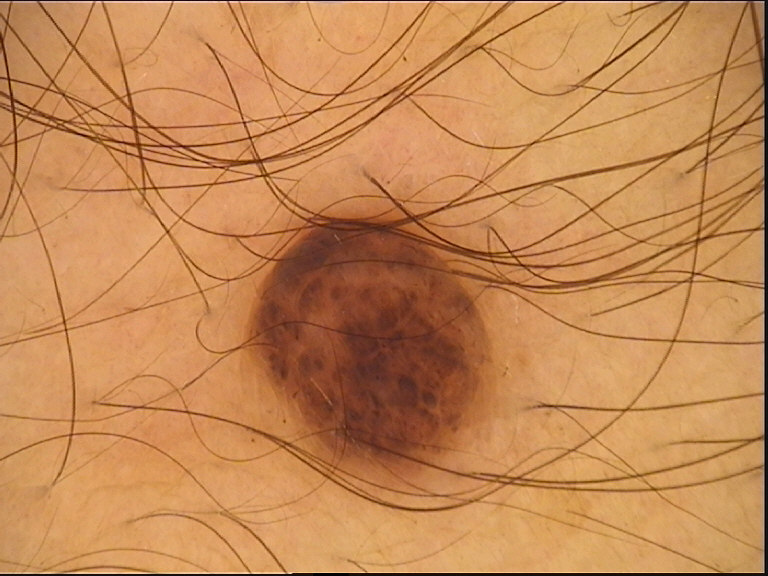modality — dermoscopy
diagnostic label — dermal nevus (expert consensus)